This image was taken at an angle · female patient, age 40–49 · the lesion involves the head or neck, arm and leg:
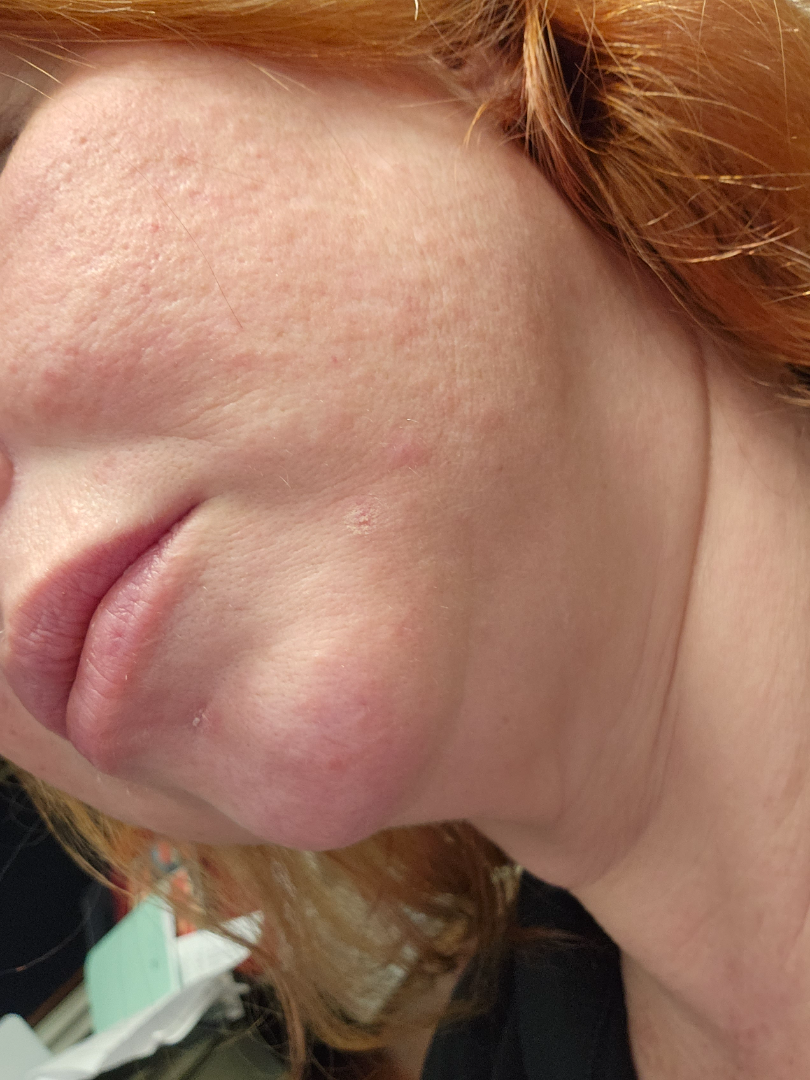* present for: one to four weeks
* texture: rough or flaky and raised or bumpy
* lesion symptoms: burning and itching
* self-categorized as: a rash
* clinical impression: most consistent with Rosacea; also raised was Rosai Dorfman disease